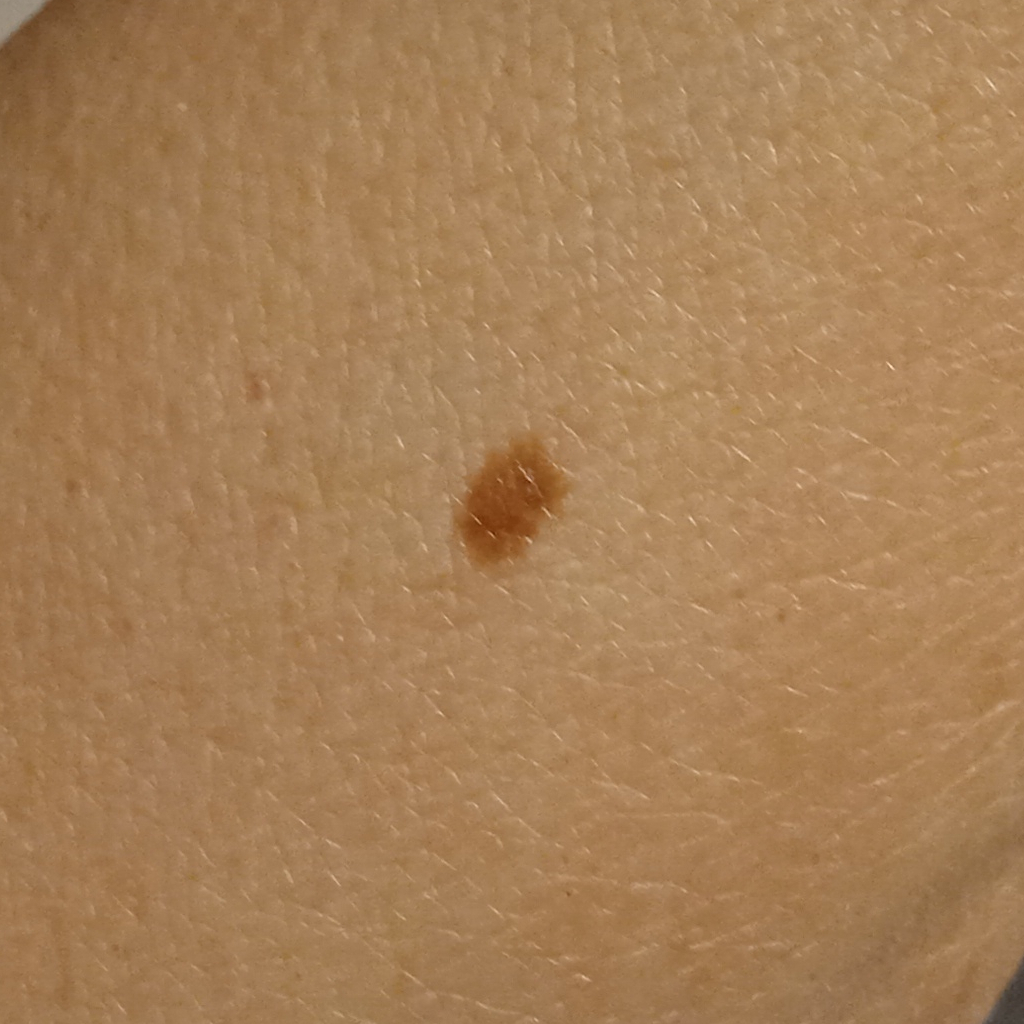Findings:
- image type — clinical photo
- subject — female, 67 years of age
- referral context — research study (no referral diagnosis)
- diameter — 4.9 mm
- diagnosis — melanocytic nevus (dermatologist consensus)